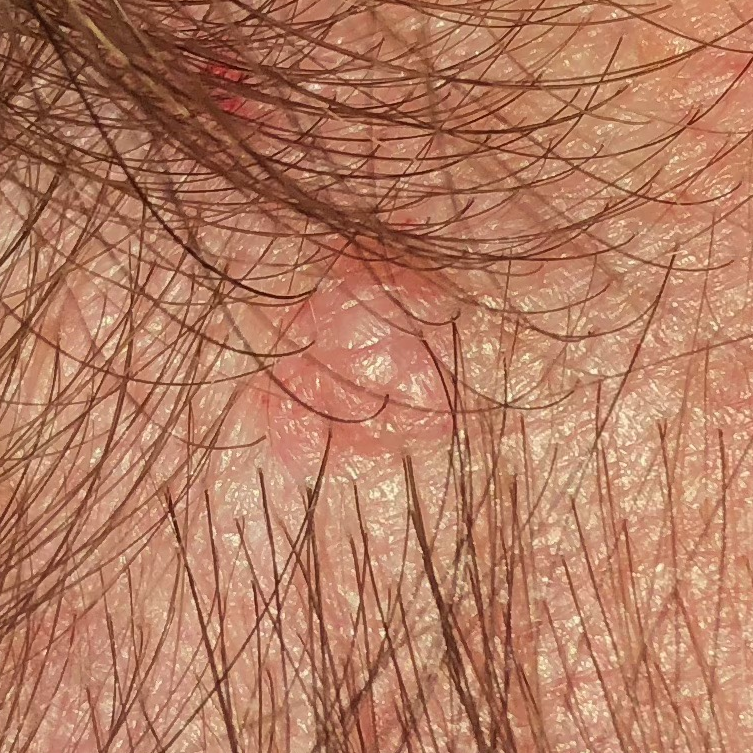<record>
<risk_factors>
<positive>prior skin cancer (patient or family)</positive>
<negative>pesticide exposure</negative>
</risk_factors>
<image>clinical photograph</image>
<lesion_location>the face</lesion_location>
<lesion_size>
<diameter_1_mm>11.0</diameter_1_mm>
<diameter_2_mm>10.0</diameter_2_mm>
</lesion_size>
<symptoms>
<present>elevation</present>
</symptoms>
<diagnosis>
<name>nevus</name>
<code>NEV</code>
<malignancy>benign</malignancy>
<confirmation>histopathology</confirmation>
</diagnosis>
</record>